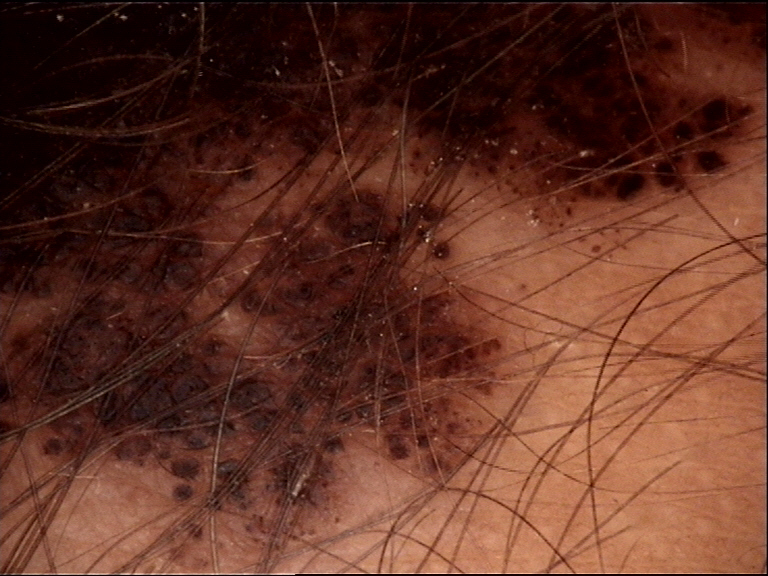imaging = dermatoscopy, class = congenital compound nevus (expert consensus).